A dermoscopic close-up of a skin lesion: 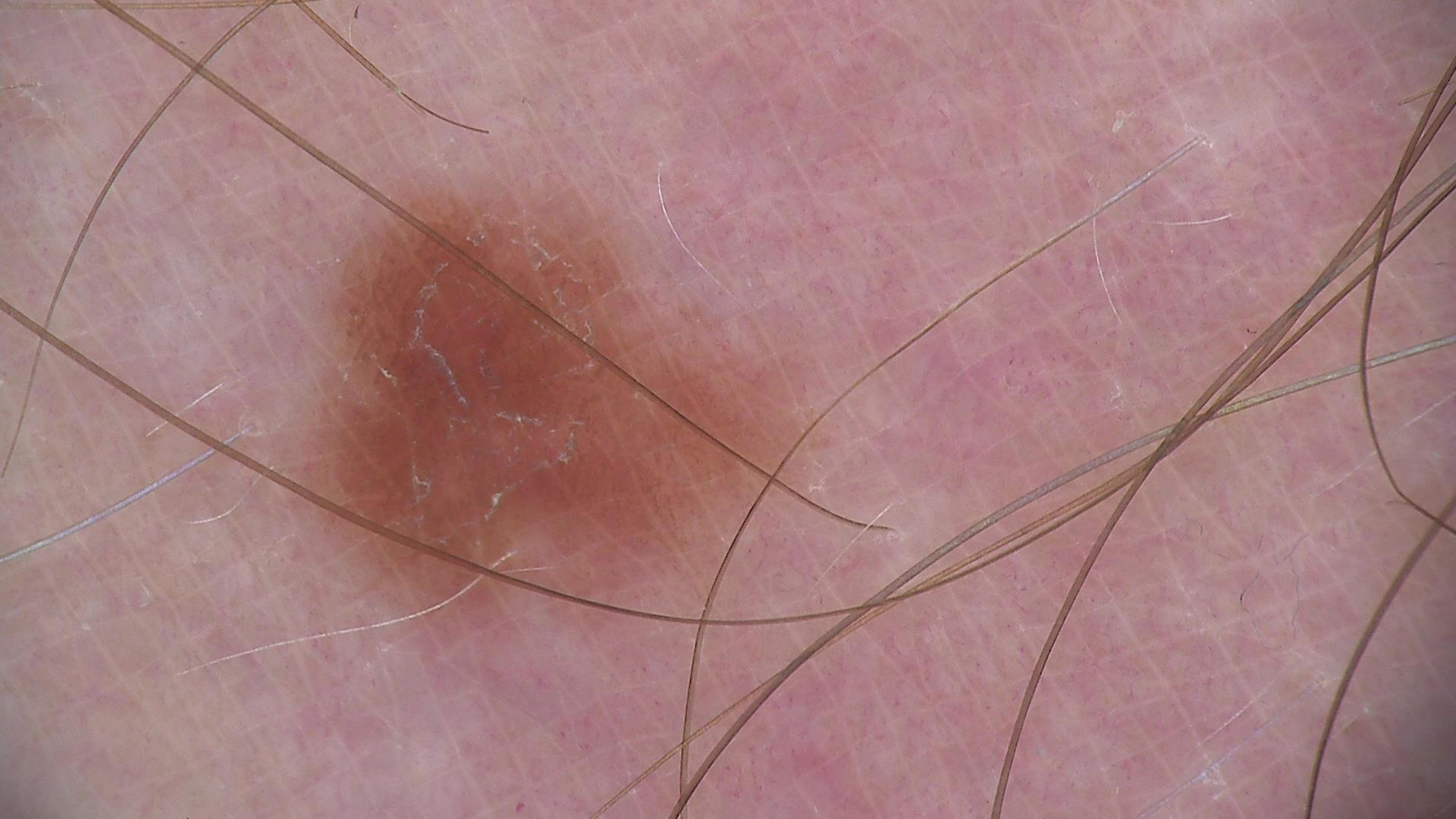{
  "diagnosis": {
    "name": "dysplastic junctional nevus",
    "code": "jd",
    "malignancy": "benign",
    "super_class": "melanocytic",
    "confirmation": "expert consensus"
  }
}